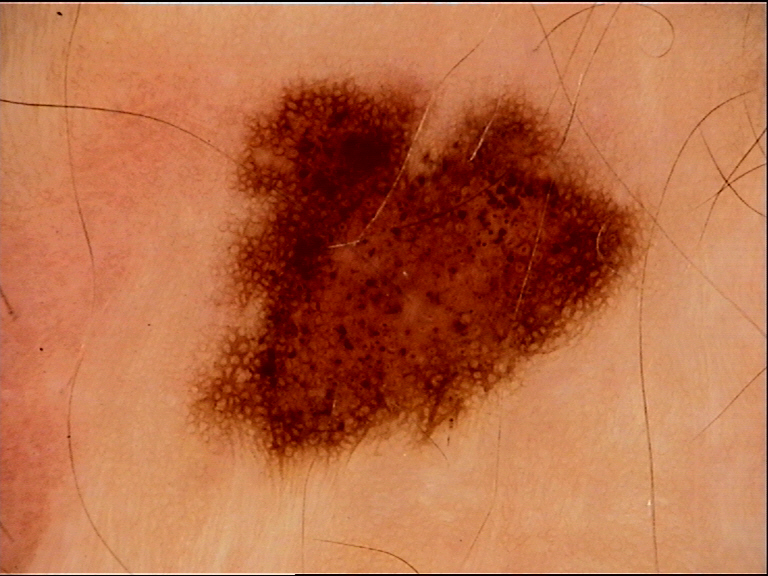• image: dermatoscopy
• diagnostic label: dysplastic junctional nevus (expert consensus)